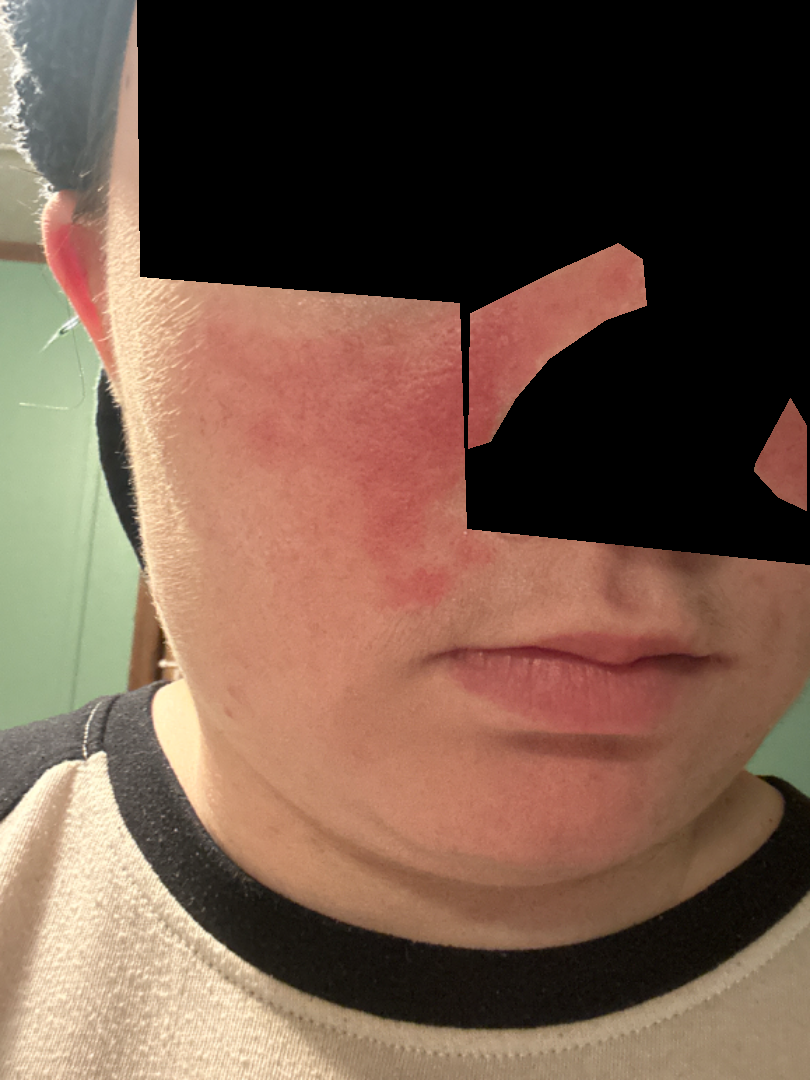Female patient, age 18–29. Texture is reported as rough or flaky. The patient reports the condition has been present for one to three months. Symptoms reported: bothersome appearance. Self-categorized by the patient as a rash. Close-up view. The head or neck is involved. On remote review of the image, the leading consideration is Rosacea; an alternative is Cutaneous lupus; less probable is Seborrheic Dermatitis; less likely is Erysipelas.